The contributor is a male aged 40–49 · the lesion involves the top or side of the foot, leg and arm · this image was taken at an angle: 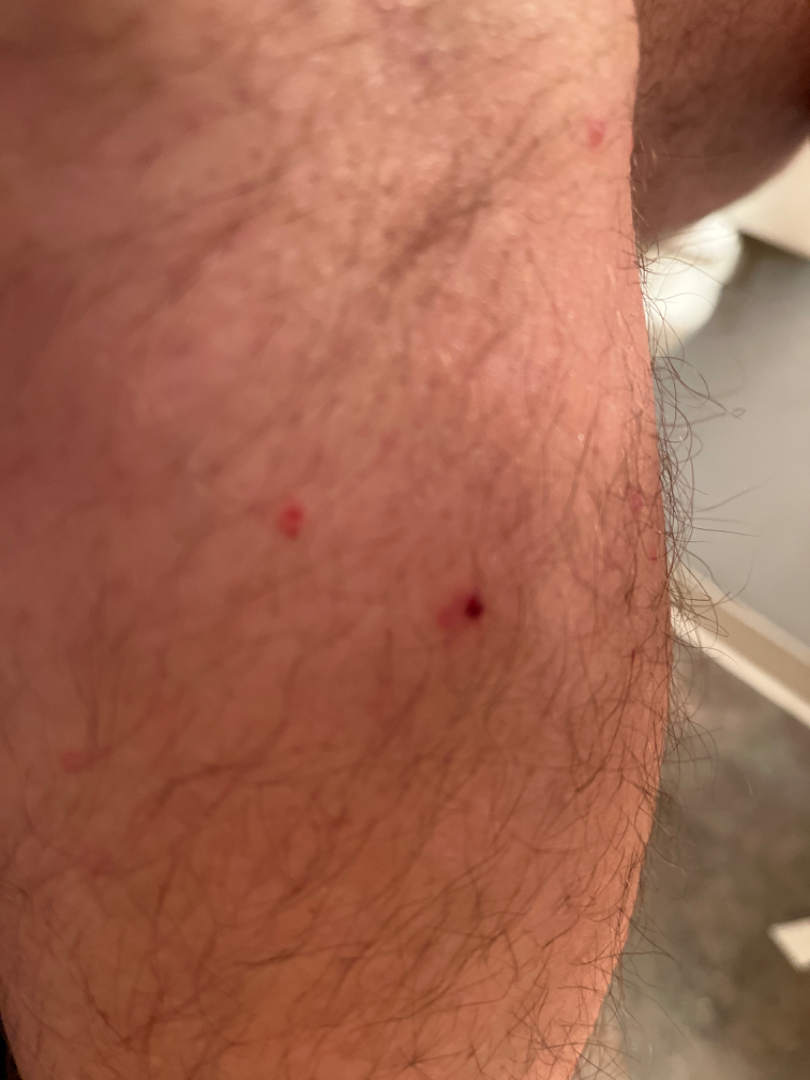Impression:
On teledermatology review: Pityriasis lichenoides (considered); Folliculitis (considered); Insect Bite (considered).